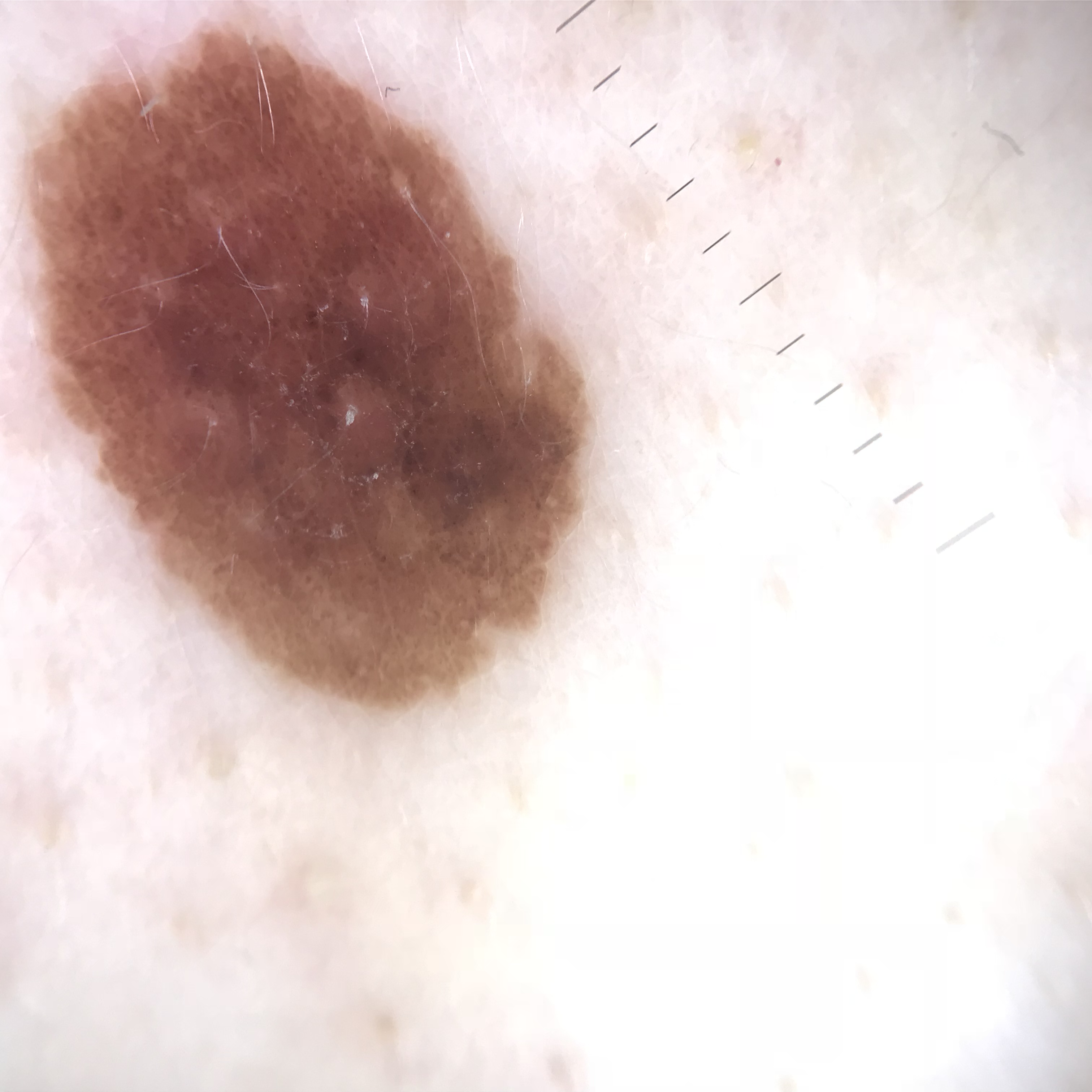{"diagnosis": {"name": "dysplastic junctional nevus", "code": "jd", "malignancy": "benign", "super_class": "melanocytic", "confirmation": "expert consensus"}}